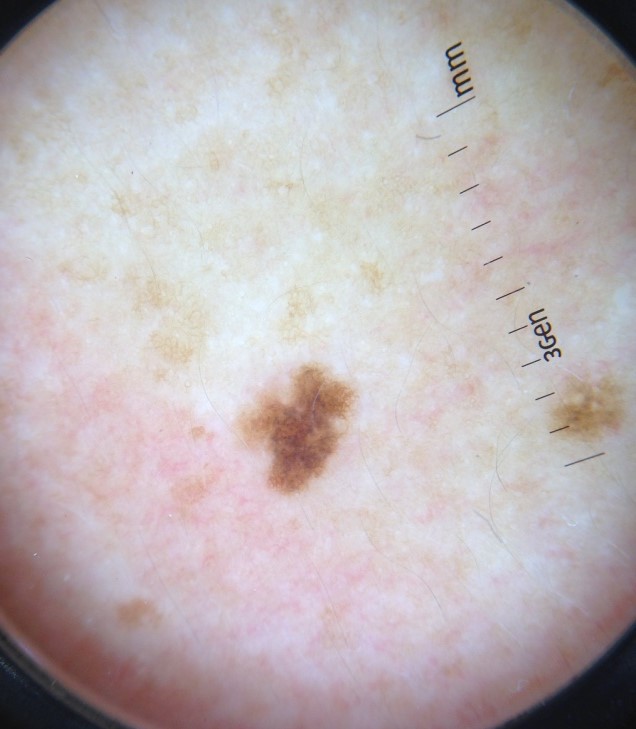Conclusion:
Classified as a benign lesion — a dysplastic junctional nevus.